Male subject, age 50–59; the lesion involves the front of the torso; a close-up photograph:
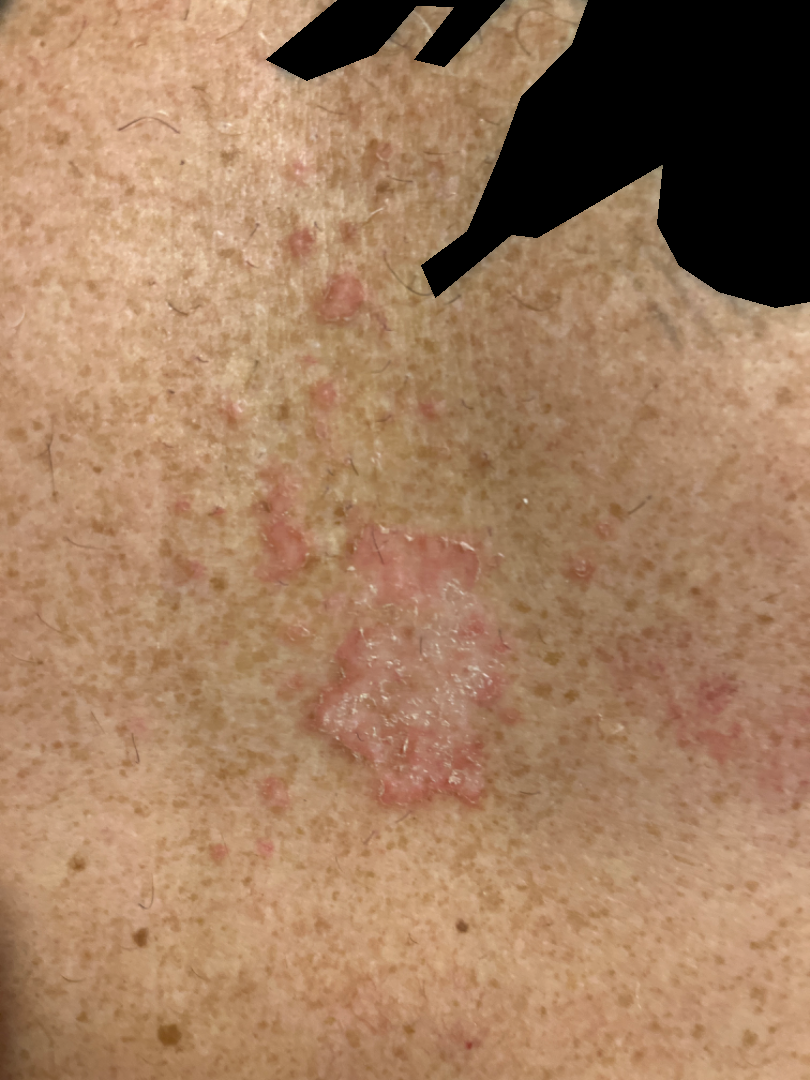  assessment: could not be assessed